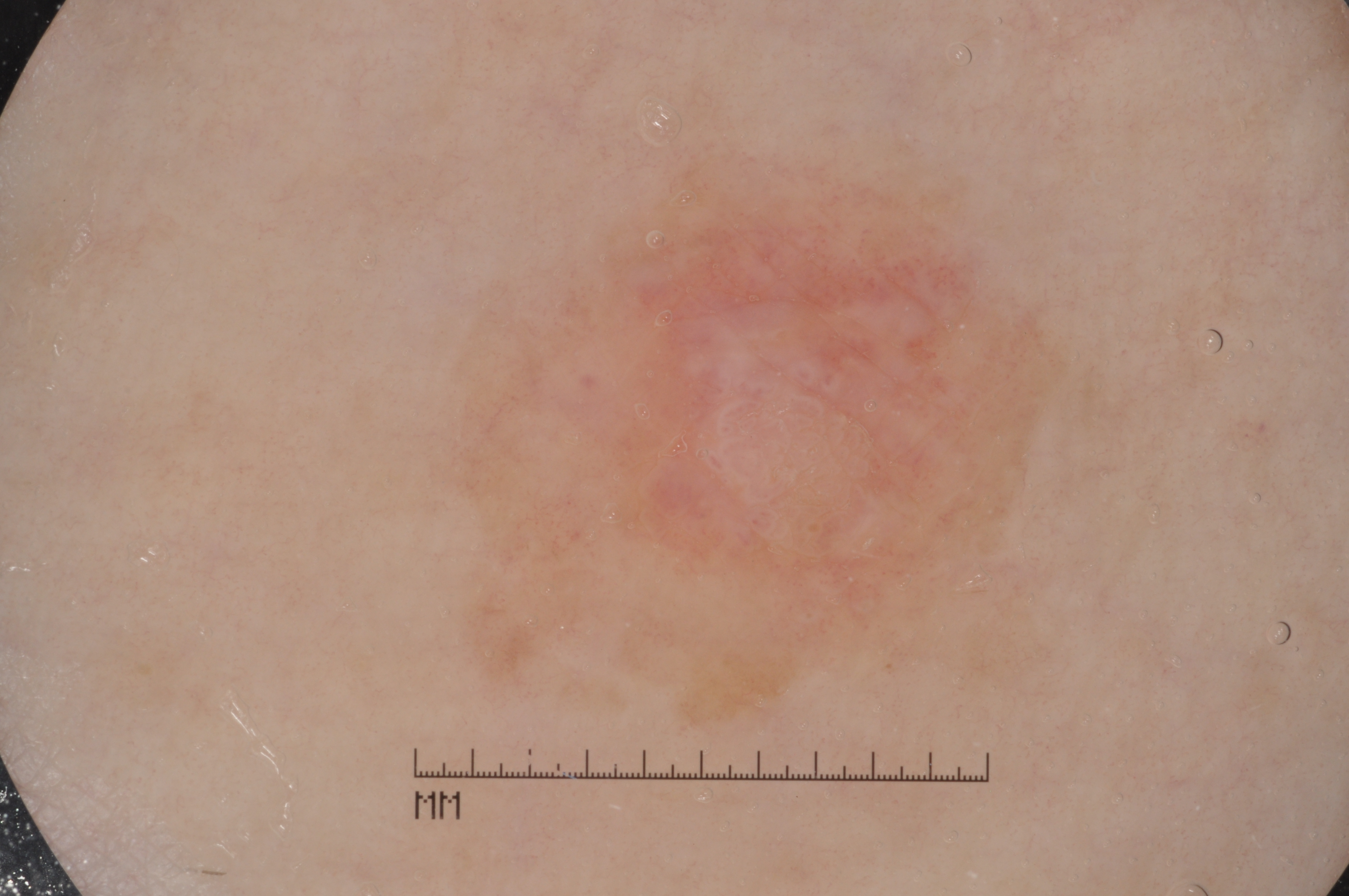A dermoscopic close-up of a skin lesion.
A female subject, in their mid-70s.
A mid-sized lesion within the field.
With coordinates (x1, y1, x2, y2), the lesion is bounded by <box>409, 118, 1080, 767</box>.
Dermoscopically, the lesion shows milia-like cysts; no streaks, pigment network, or negative network.
The lesion was assessed as a seborrheic keratosis, a lesion of keratinocytic origin.